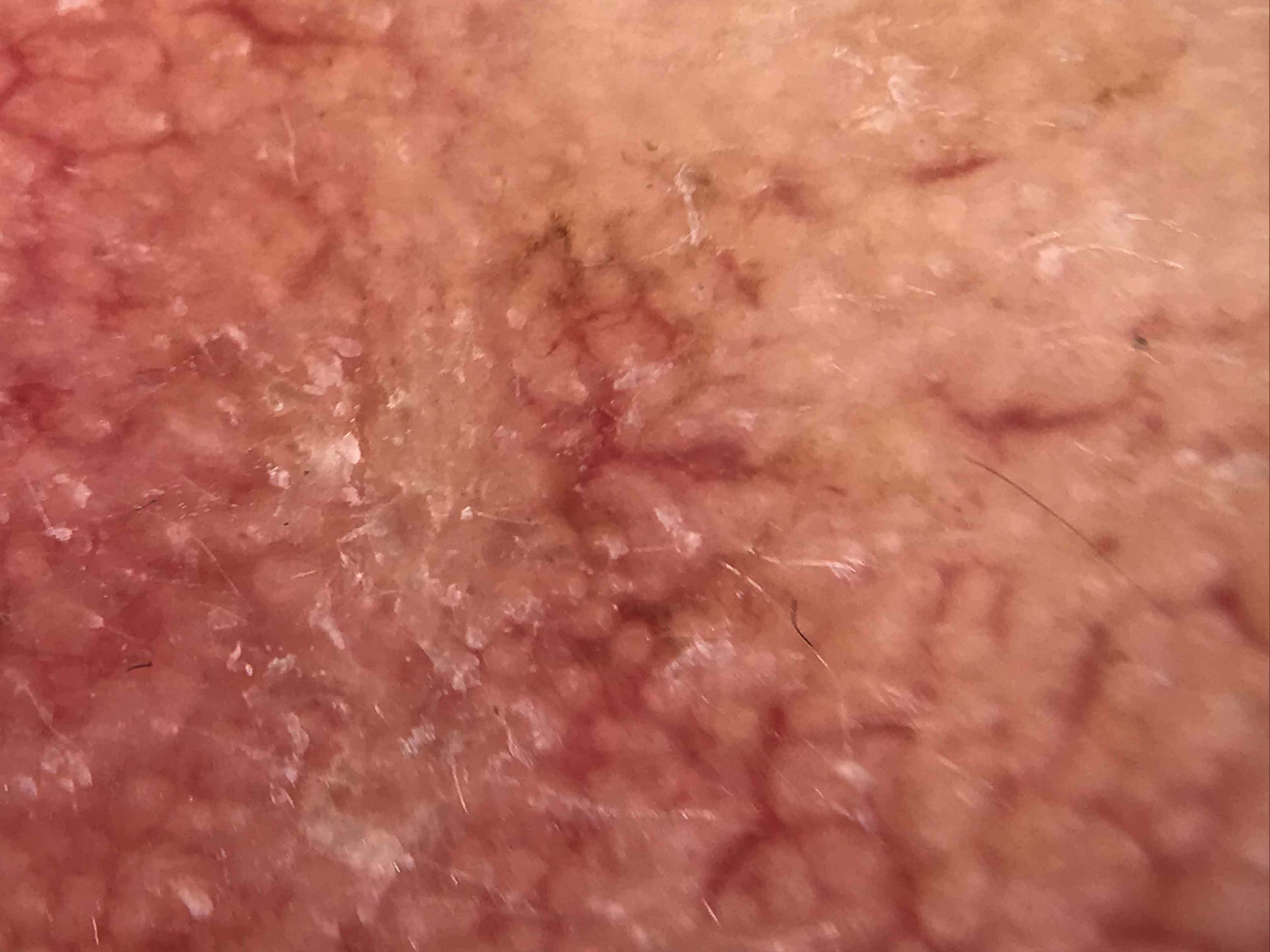Summary: A dermoscopic photograph of a skin lesion. Impression: Classified as a keratinocytic lesion — a seborrheic keratosis.